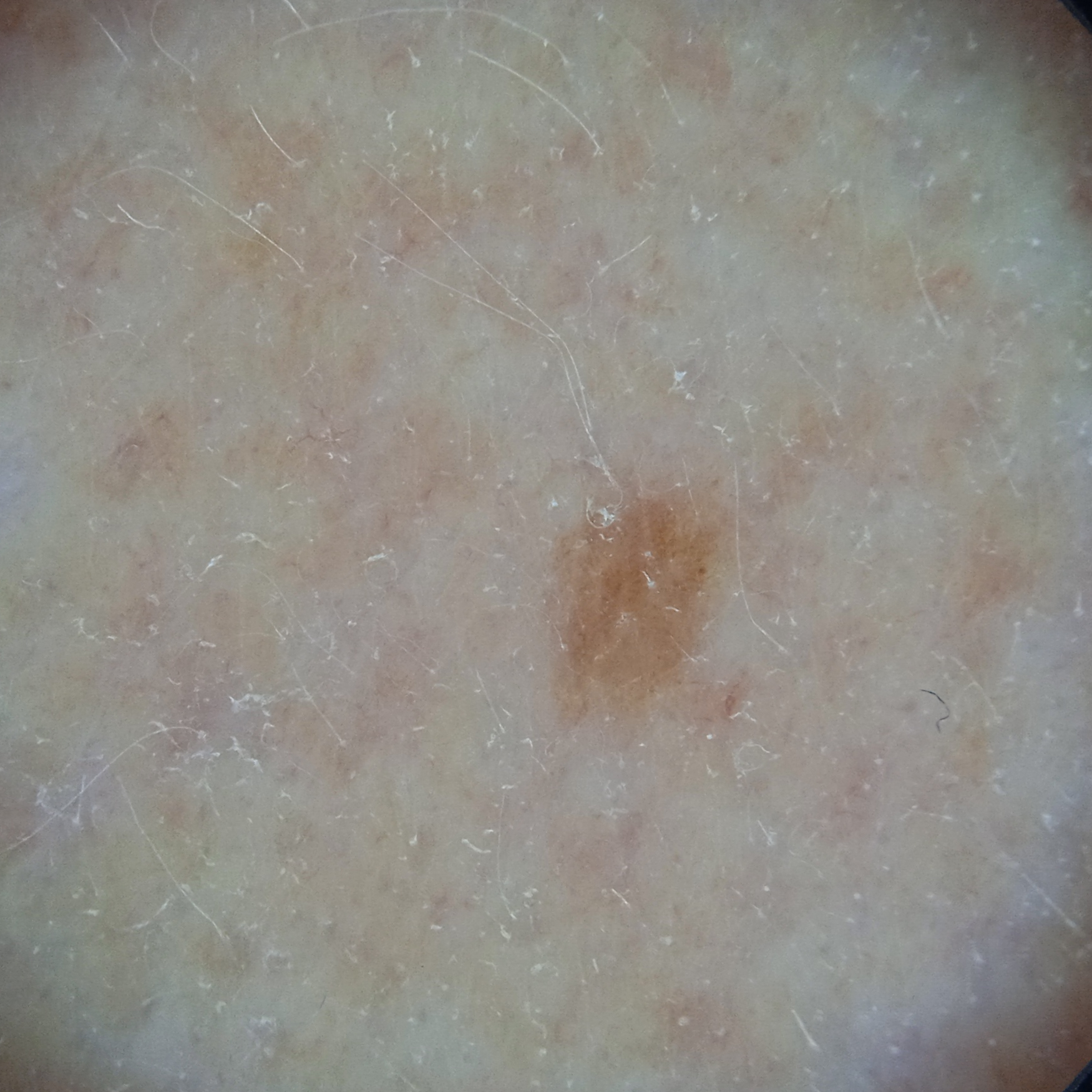Q: What was the diagnosis?
A: melanocytic nevus (dermatologist consensus)